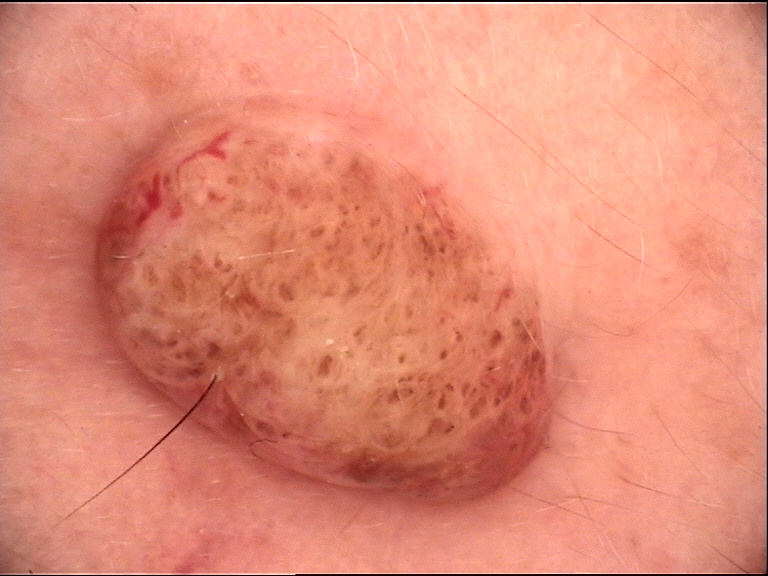Findings:
A skin lesion imaged with a dermatoscope.
Impression:
The diagnosis was a dermal nevus.